The patient is a female aged 30–39. This is a close-up image. The leg is involved.
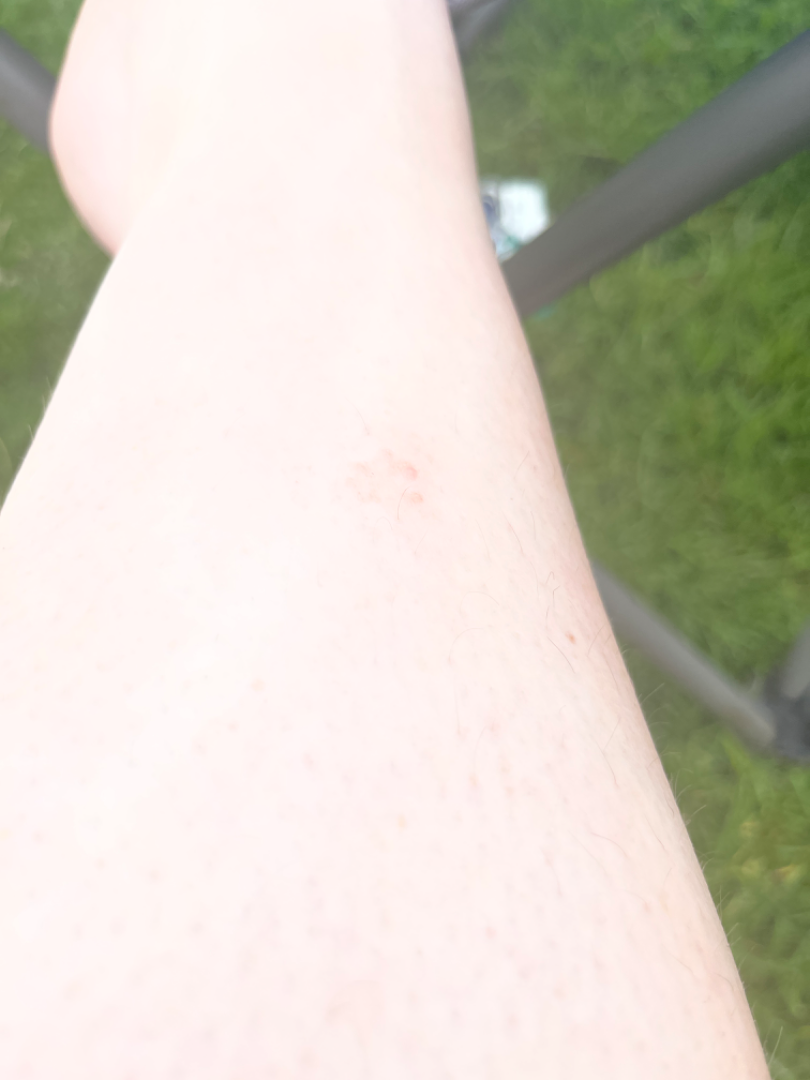assessment: indeterminate from the photograph, skin tone: self-reported Fitzpatrick skin type III; lay reviewers estimated Monk Skin Tone 1 or 2 (two reviewer pools), systemic symptoms: none reported, self-categorized as: a rash, present for: one to three months, lesion symptoms: bothersome appearance.